The photograph is a close-up of the affected area:
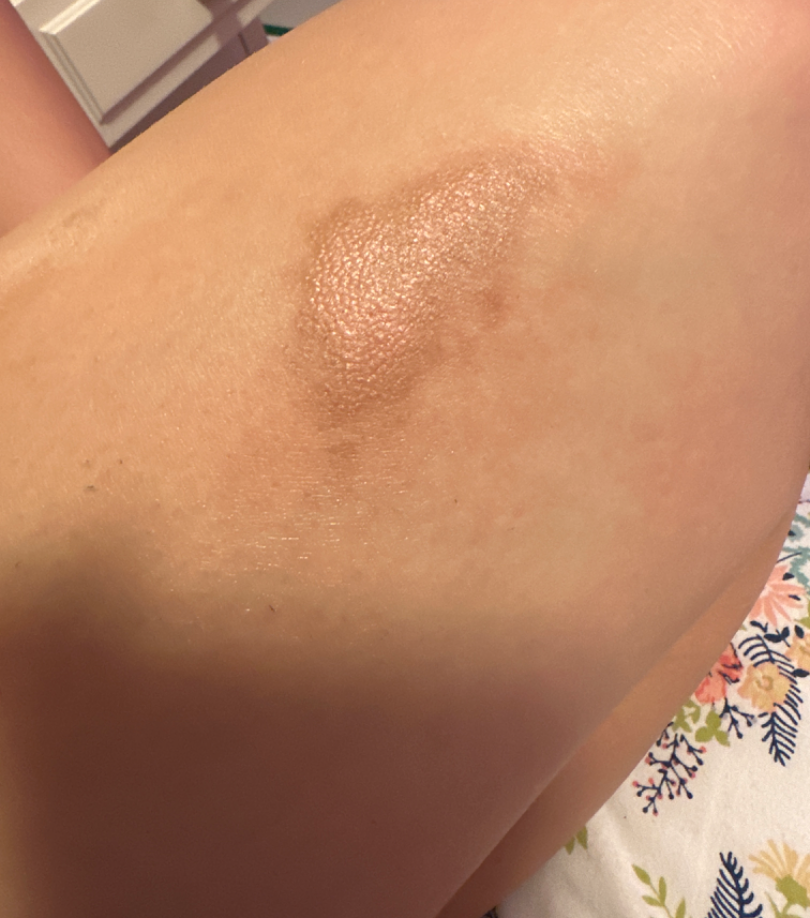<report>
  <assessment>indeterminate</assessment>
</report>